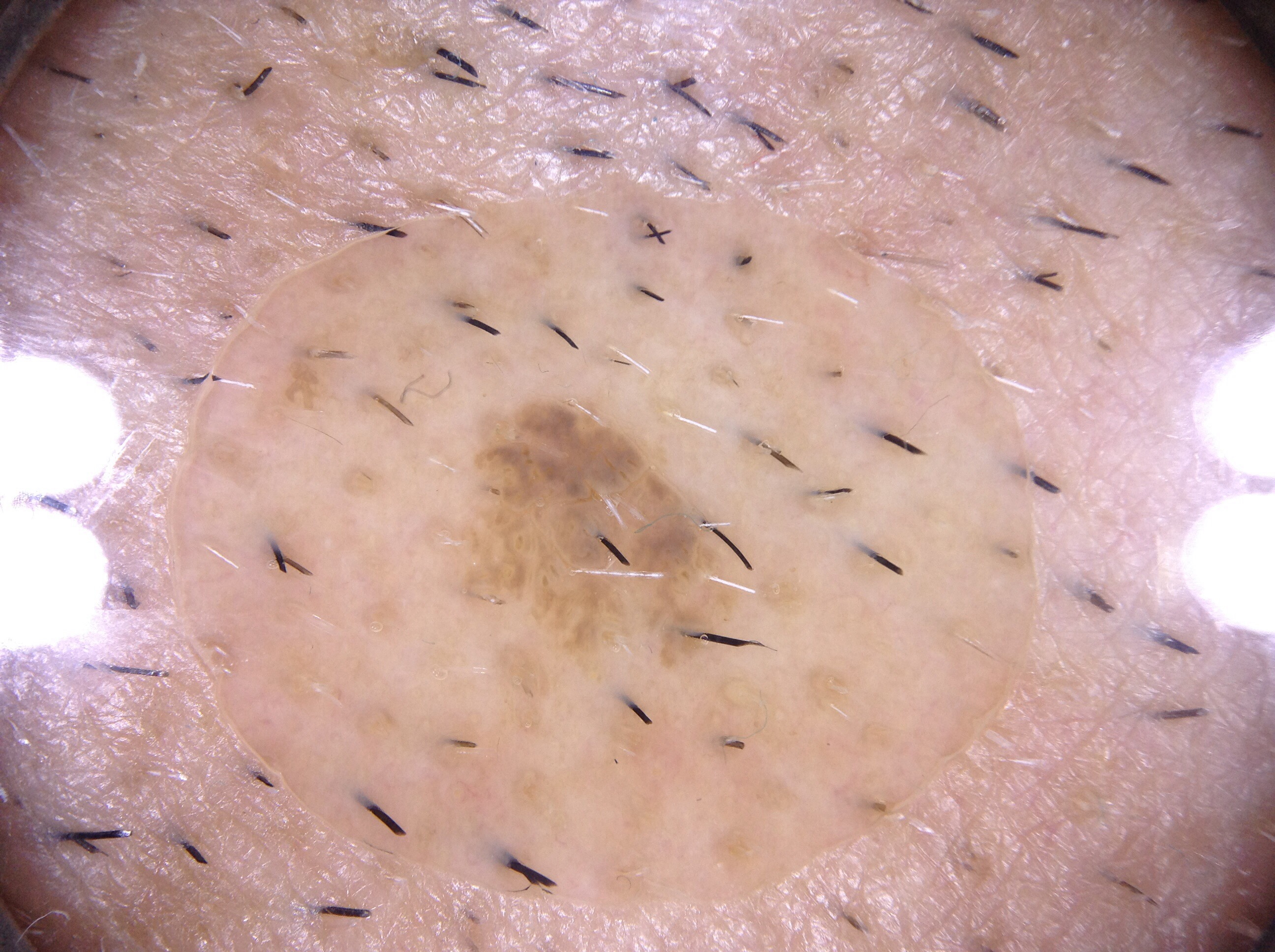A male patient approximately 60 years of age.
A dermoscopic image of a skin lesion.
The lesion is small relative to the field of view.
In (x1, y1, x2, y2) order, the visible lesion spans bbox(456, 396, 744, 677).
The dermoscopic pattern shows no milia-like cysts, pigment network, negative network, or streaks.
The clinical diagnosis was a seborrheic keratosis, a benign lesion.